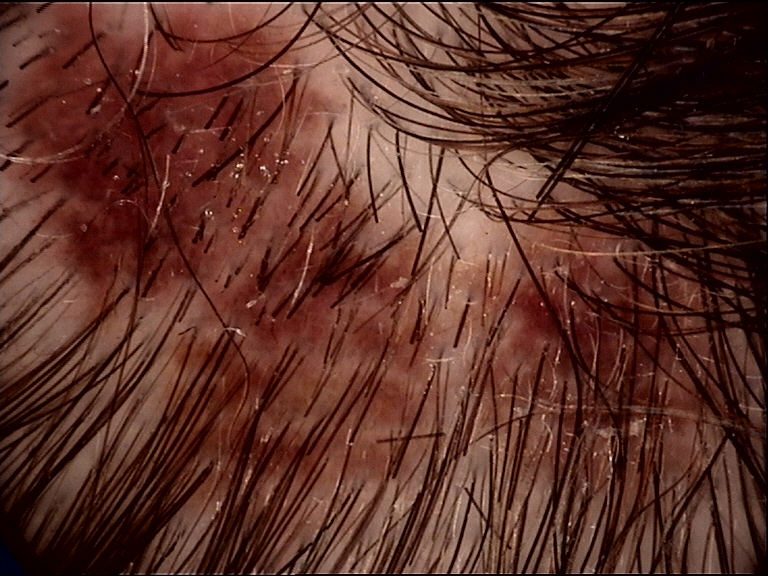diagnosis:
  name: dysplastic junctional nevus
  code: jd
  malignancy: benign
  super_class: melanocytic
  confirmation: expert consensus